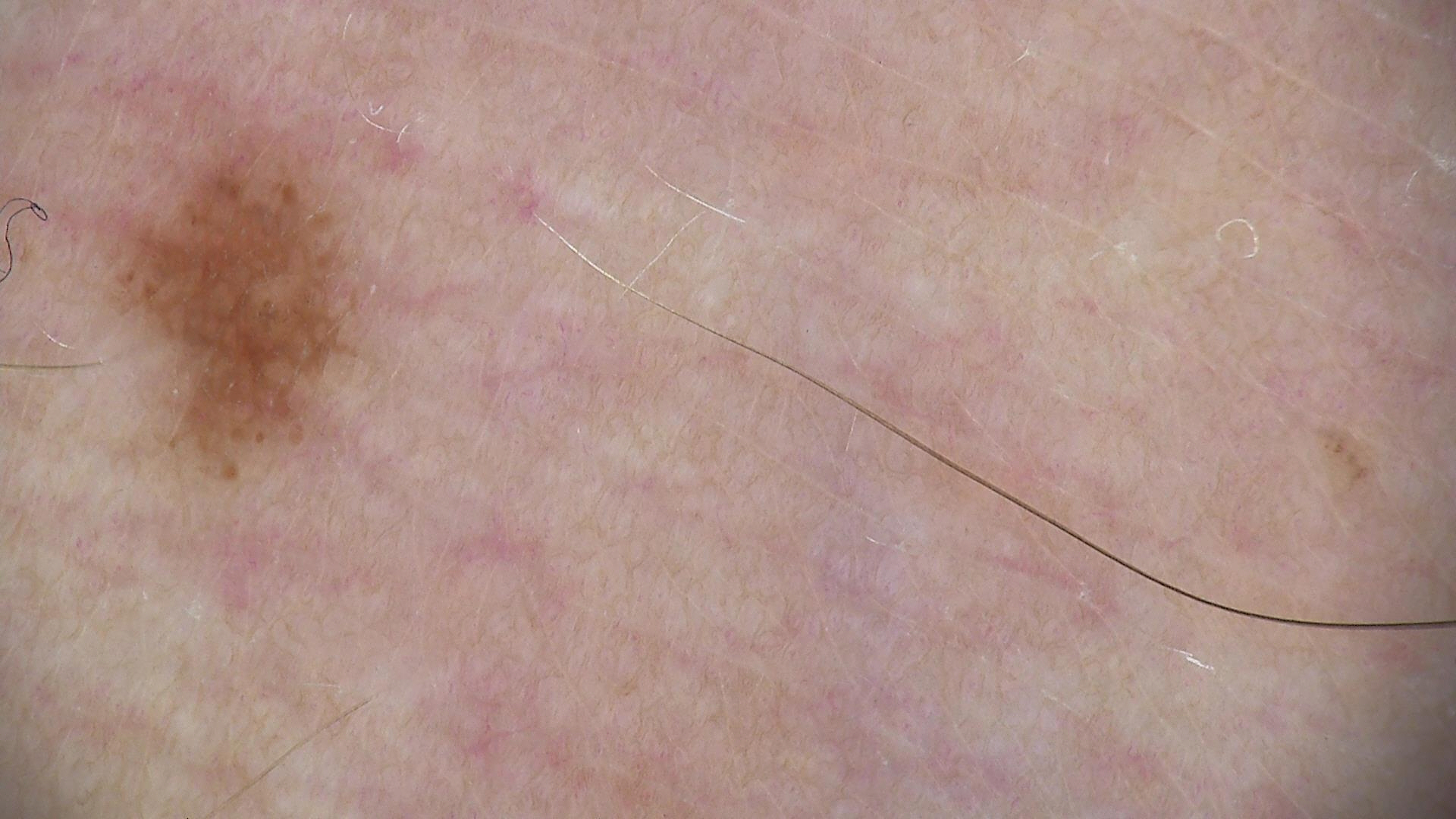Q: What is this lesion?
A: dysplastic junctional nevus (expert consensus)